A dermoscopy image of a single skin lesion.
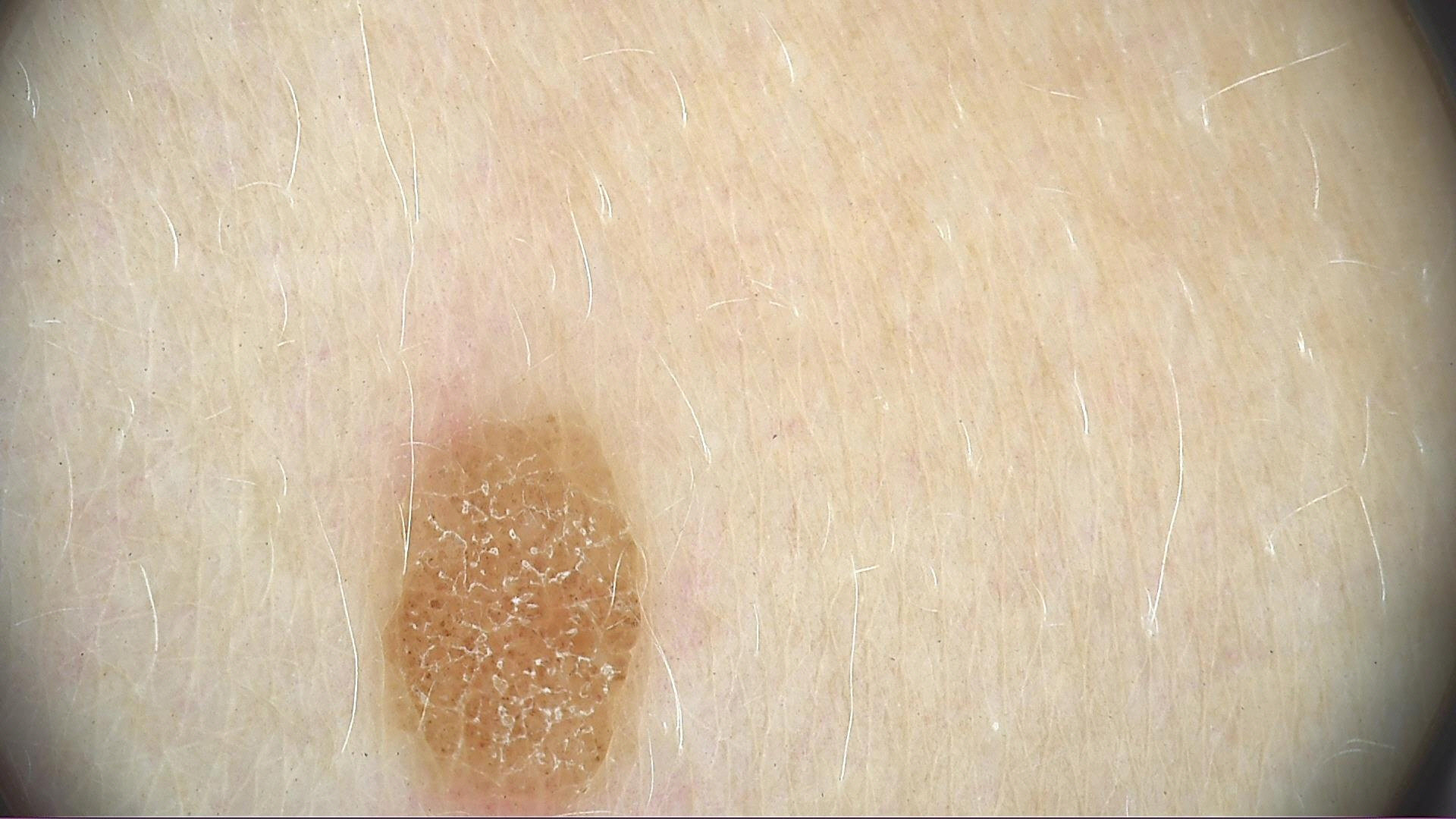The diagnostic label was a compound nevus.